A skin lesion imaged with a dermatoscope.
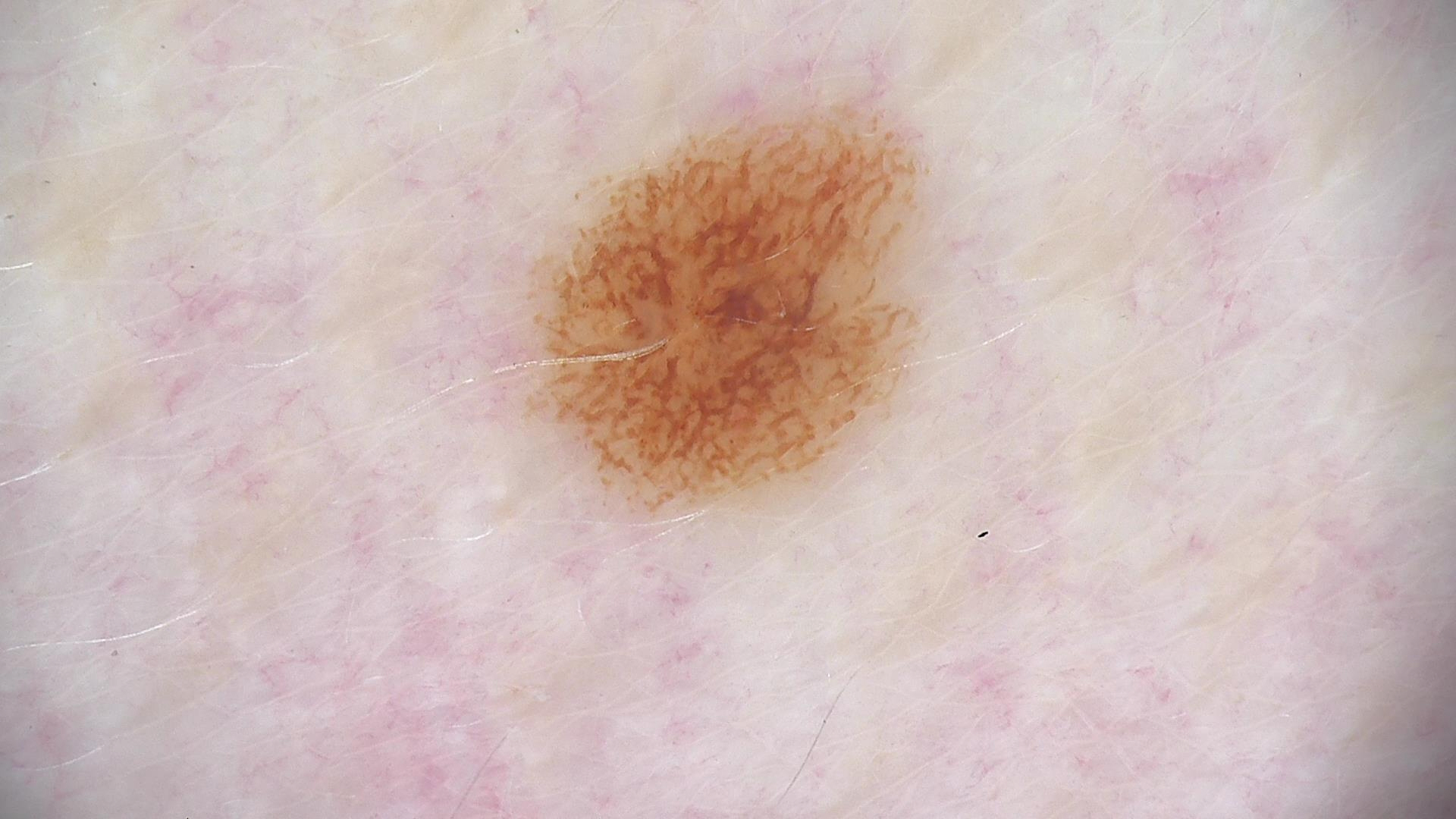Impression: Consistent with a dysplastic junctional nevus.